The leg is involved · the photograph was taken at a distance · female subject, age 40–49: 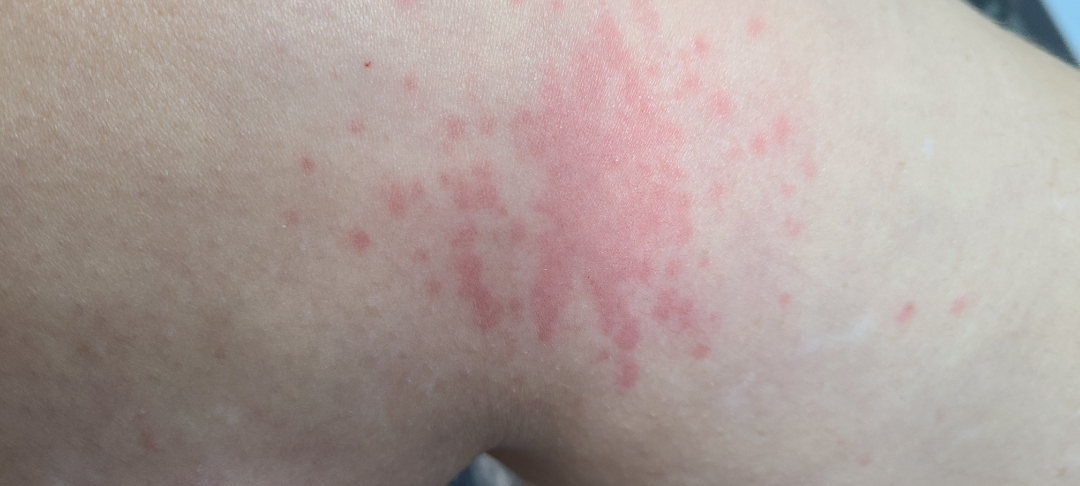texture — raised or bumpy
skin tone — Fitzpatrick phototype III; lay reviewers estimated Monk Skin Tone 3–4
patient-reported symptoms — itching and bothersome appearance
patient describes the issue as — a rash
symptom duration — about one day
differential — the impression was split between Urticaria, Insect Bite and Allergic Contact Dermatitis